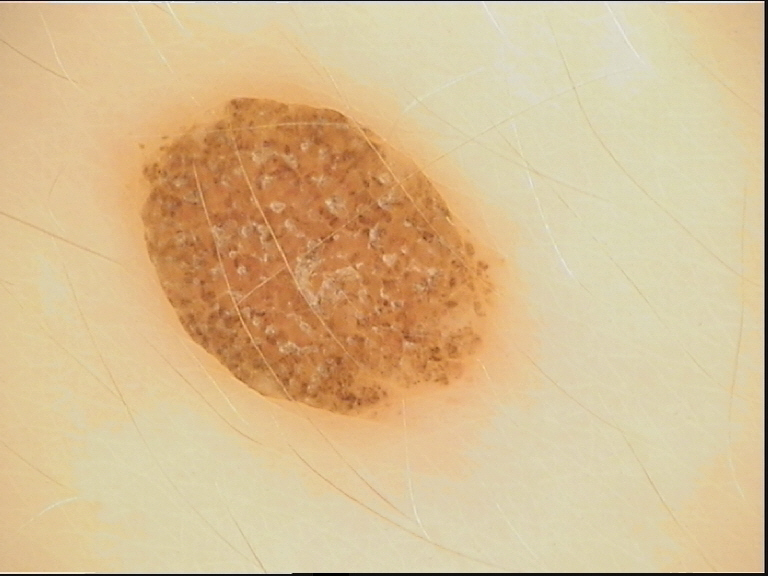{
  "diagnosis": {
    "name": "dermal nevus",
    "code": "db",
    "malignancy": "benign",
    "super_class": "melanocytic",
    "confirmation": "expert consensus"
  }
}